A dermoscopic photograph of a skin lesion:
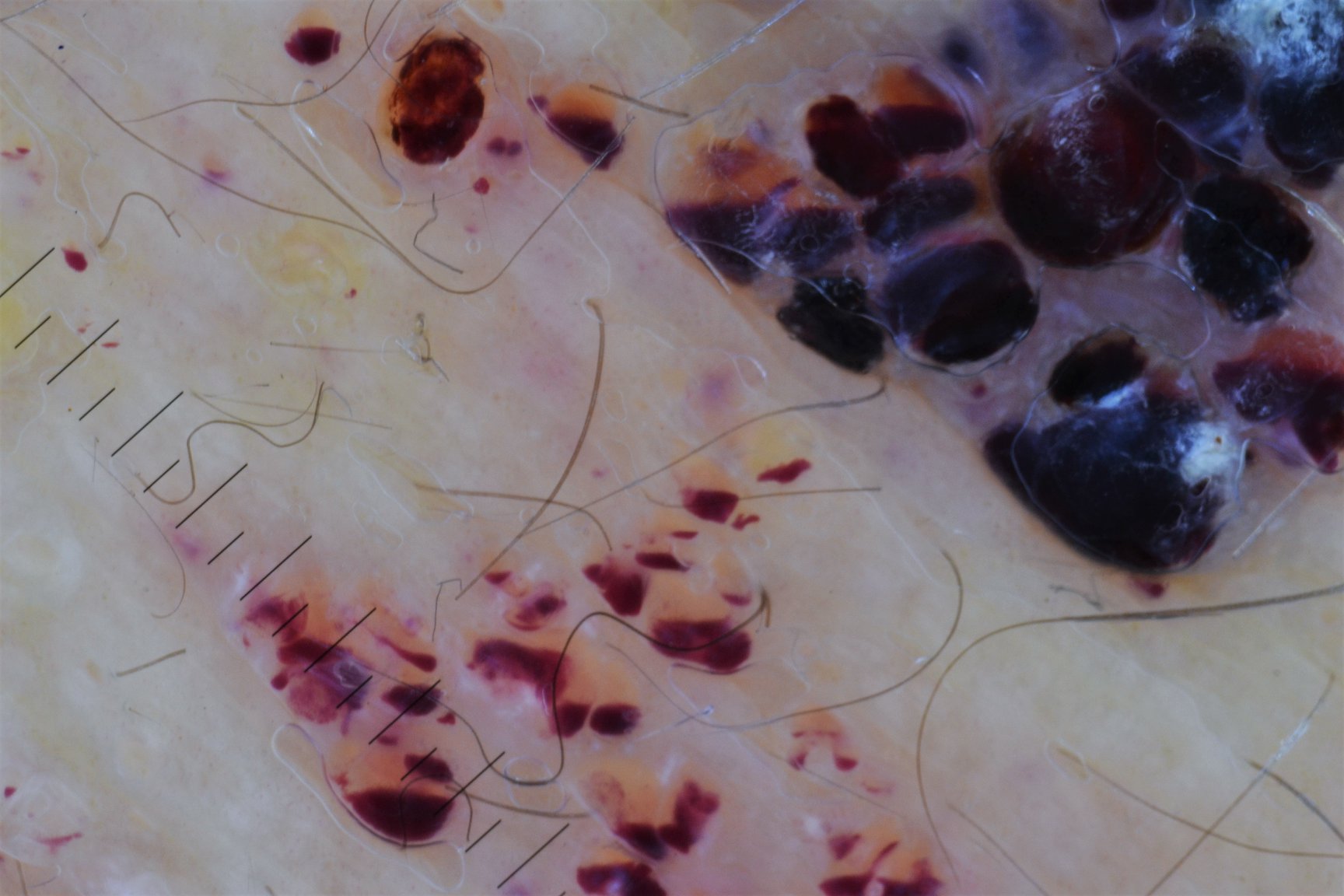| field | value |
|---|---|
| category | vascular |
| assessment | lymphangioma (expert consensus) |